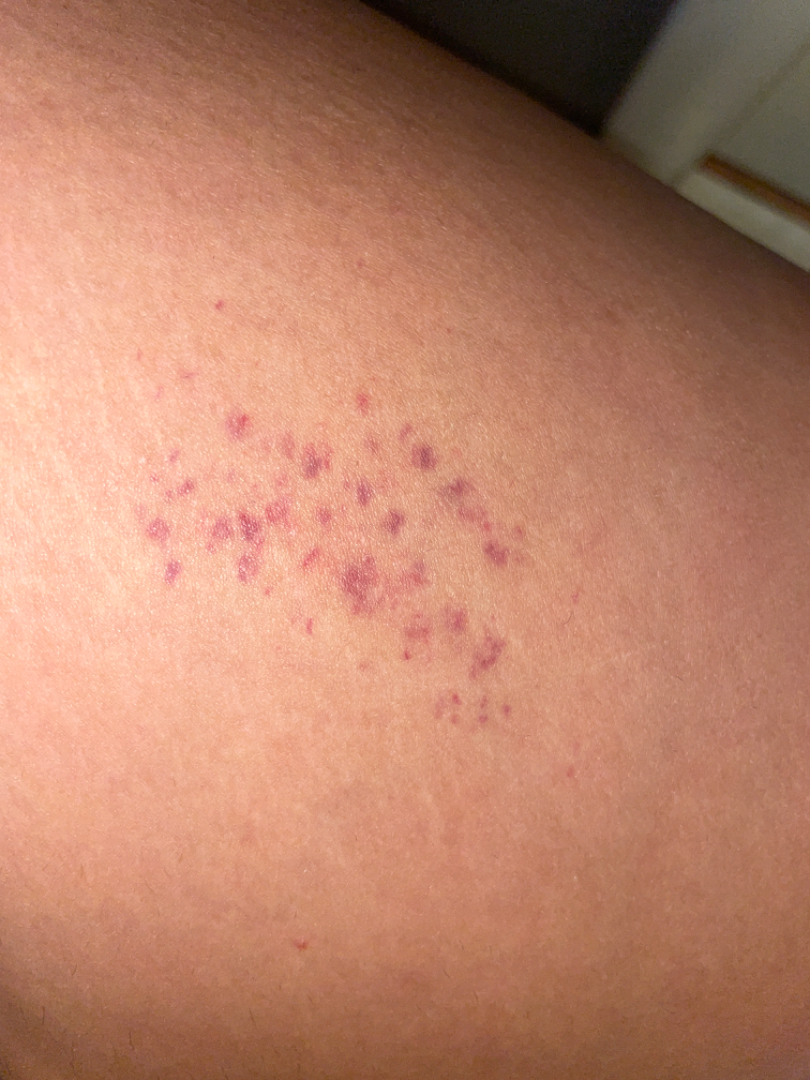assessment: unable to determine
lesion symptoms: bothersome appearance and itching
patient describes the issue as: a rash
lesion texture: flat
anatomic site: leg
contributor: female, age 18–29
shot type: close-up